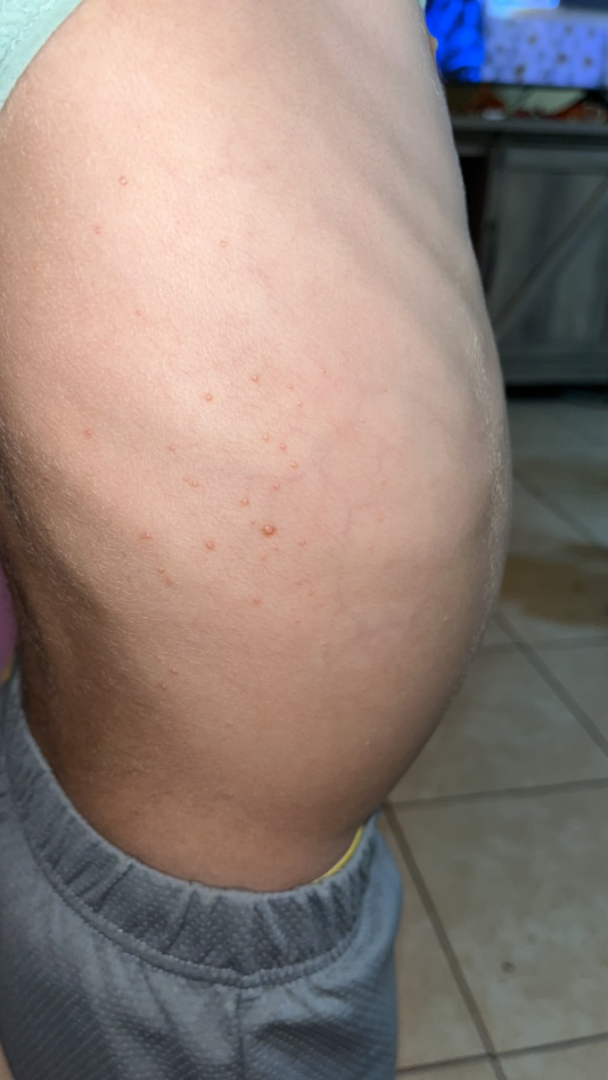| field | value |
|---|---|
| assessment | unable to determine |
| skin tone | Fitzpatrick III |
| affected area | back of the torso and front of the torso |
| lesion texture | fluid-filled and raised or bumpy |
| image framing | close-up |
| duration | about one day |